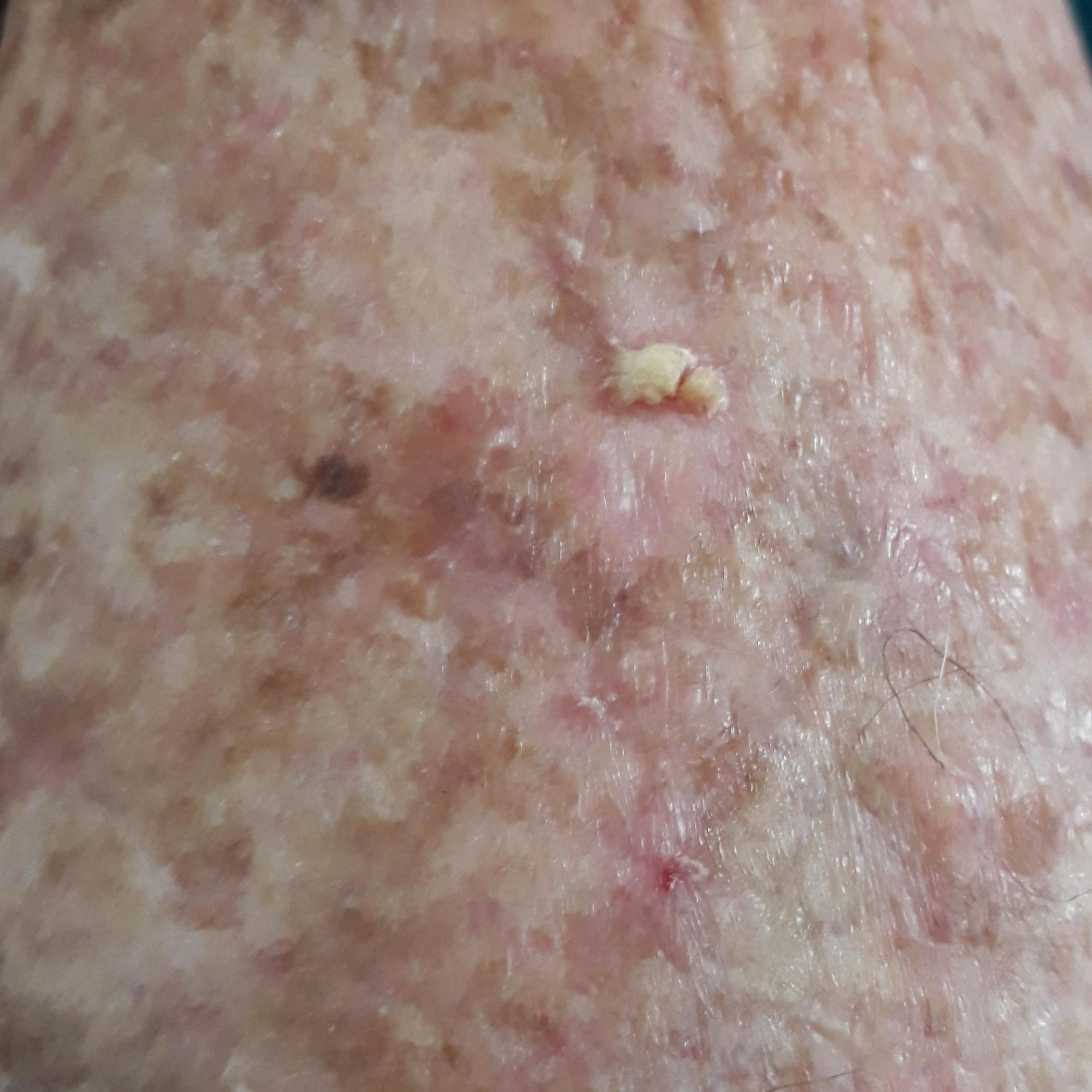A female subject in their 90s.
A clinical photograph showing a skin lesion.
Recorded as Fitzpatrick phototype I.
The chart records prior malignancy (patient or family) and no prior skin cancer (patient or family).
The lesion was found on a forearm.
The lesion measures 13 × 7 mm.
Per patient report, the lesion itches, has bled, hurts, and is elevated, but has not grown and has not changed.
The diagnostic impression was an actinic keratosis.